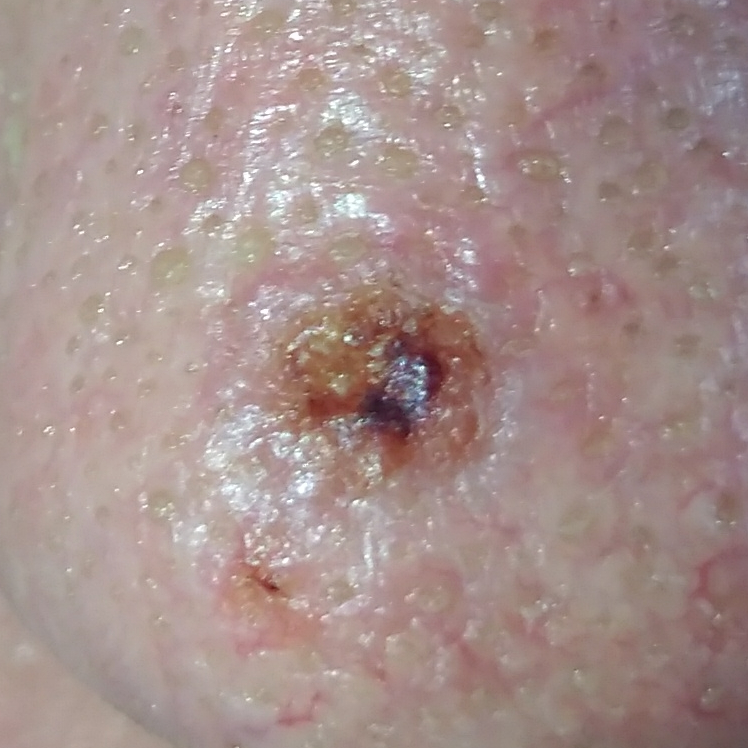{"patient": {"age": 40, "gender": "male"}, "lesion_location": "the chest", "symptoms": {"present": ["bleeding", "itching", "elevation", "pain", "growth"], "absent": ["change in appearance"]}, "diagnosis": {"name": "basal cell carcinoma", "code": "BCC", "malignancy": "malignant", "confirmation": "histopathology"}}